A dermatoscopic image of a skin lesion.
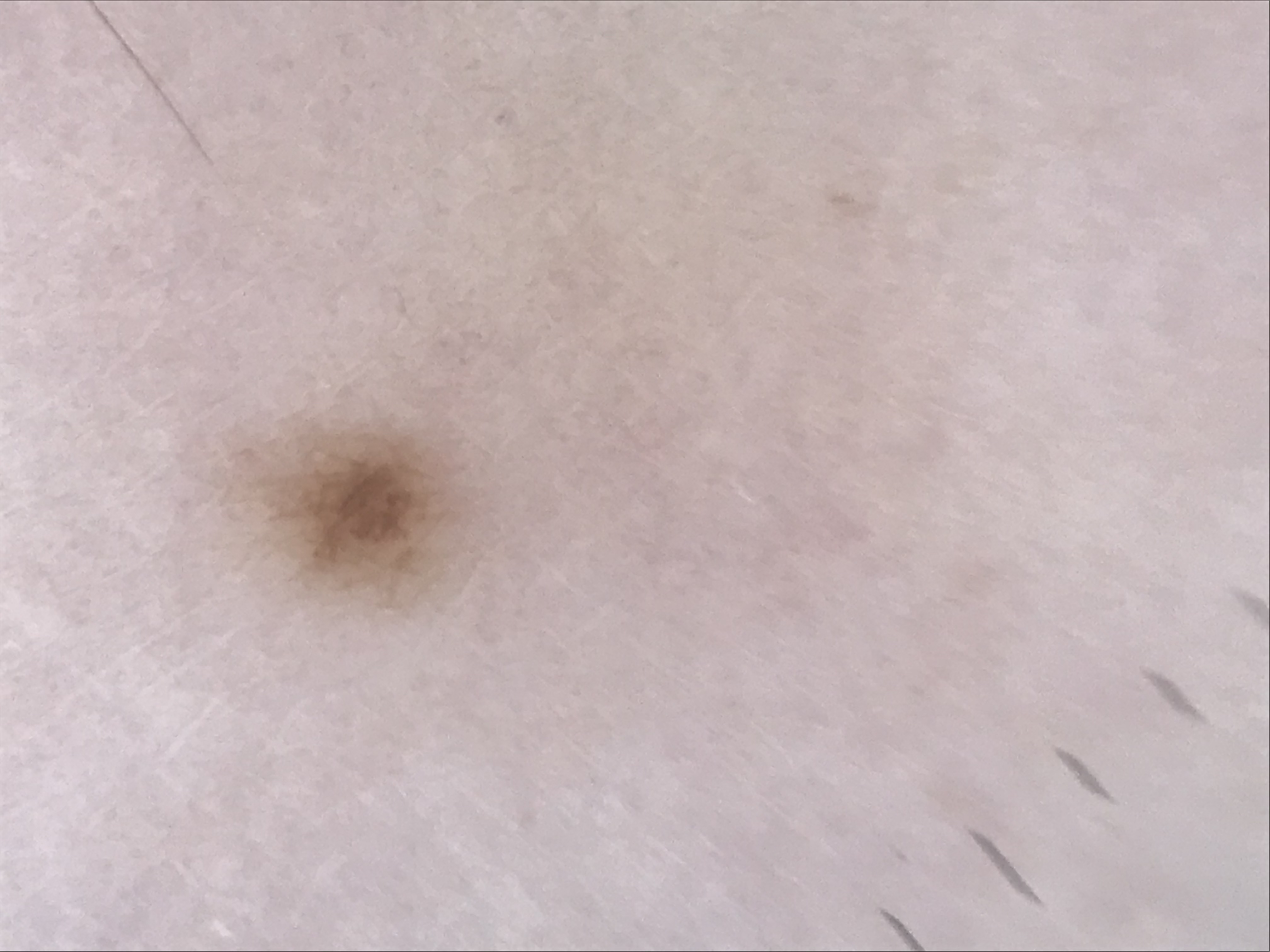diagnosis = junctional nevus (expert consensus)